The affected area is the leg; an image taken at an angle.
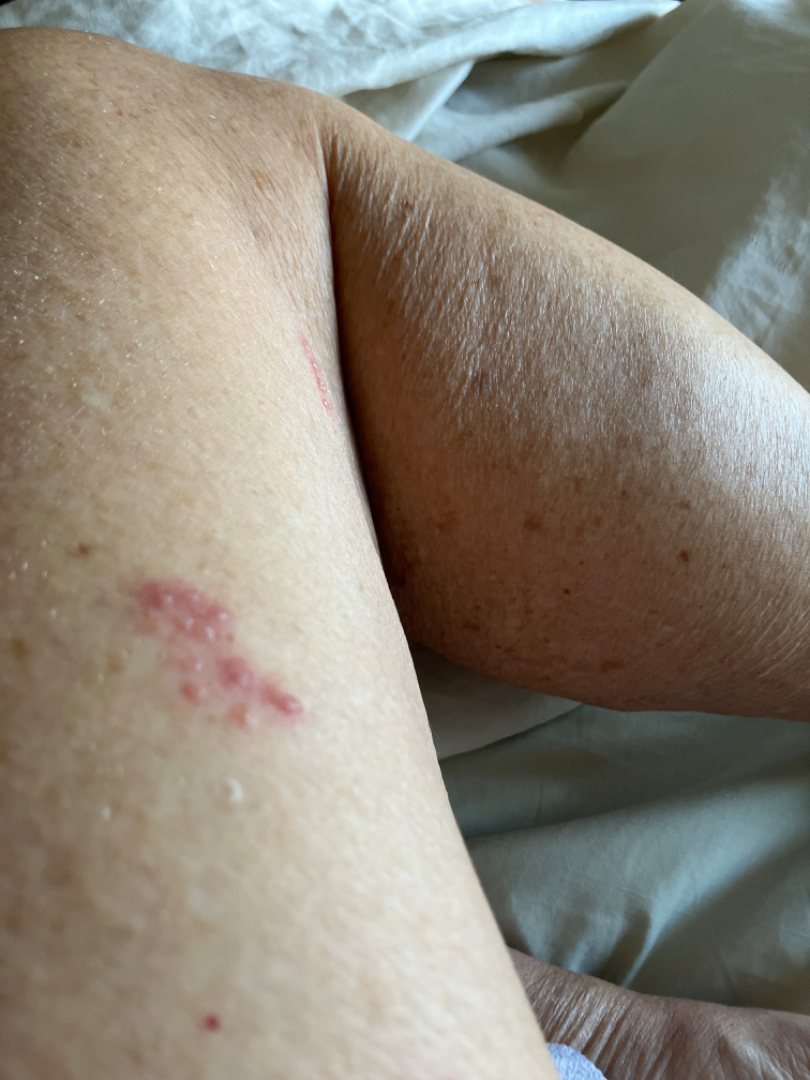The skin condition could not be confidently assessed from this image.
The patient considered this a rash.
Texture is reported as fluid-filled and raised or bumpy.
The contributor notes the condition has been present for less than one week.
Reported lesion symptoms include burning, itching and bothersome appearance.
The patient reported no systemic symptoms.